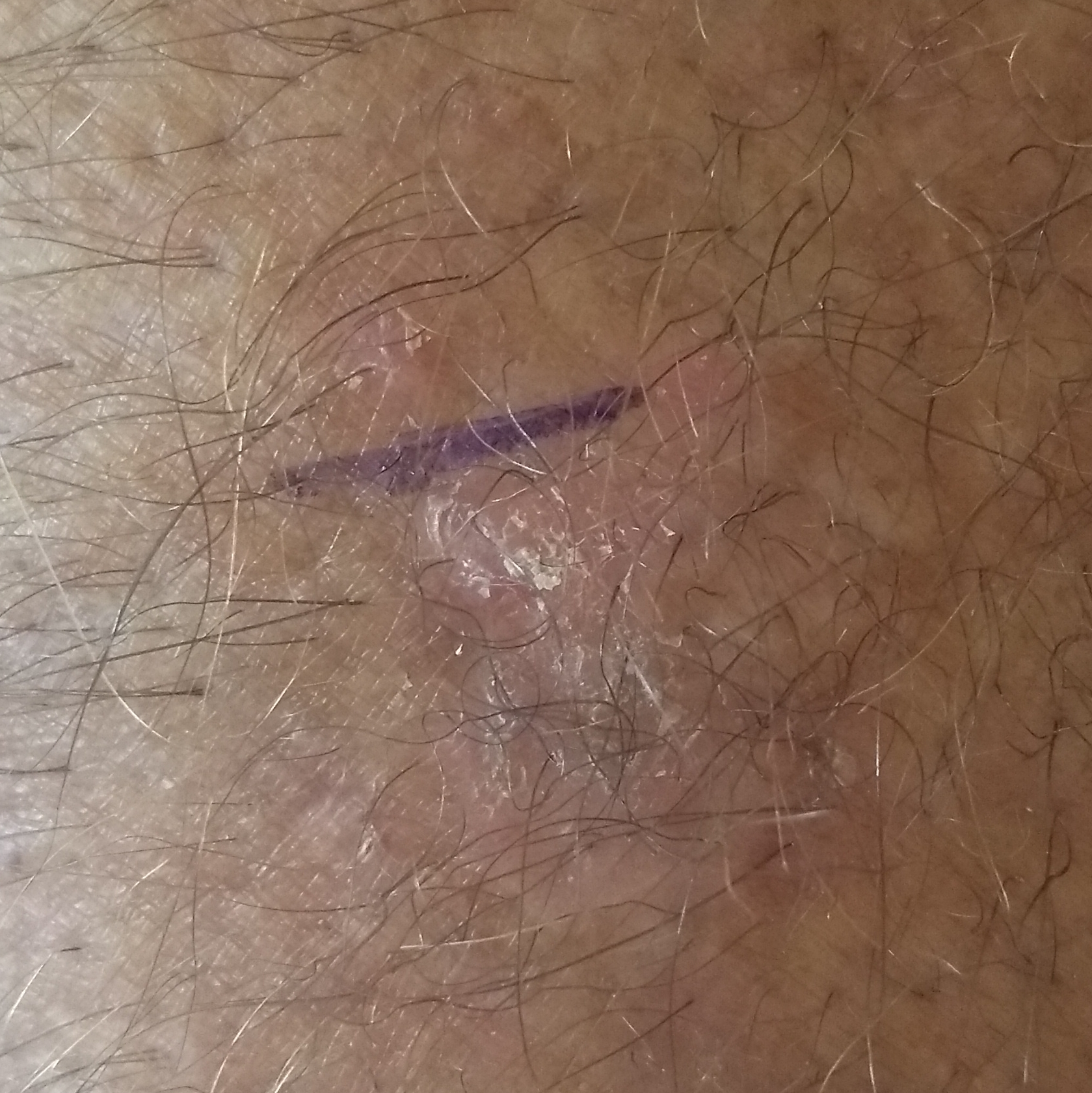image: smartphone clinical photo
anatomic site: a forearm
patient-reported symptoms: no change in appearance
diagnostic label: actinic keratosis (clinical consensus)